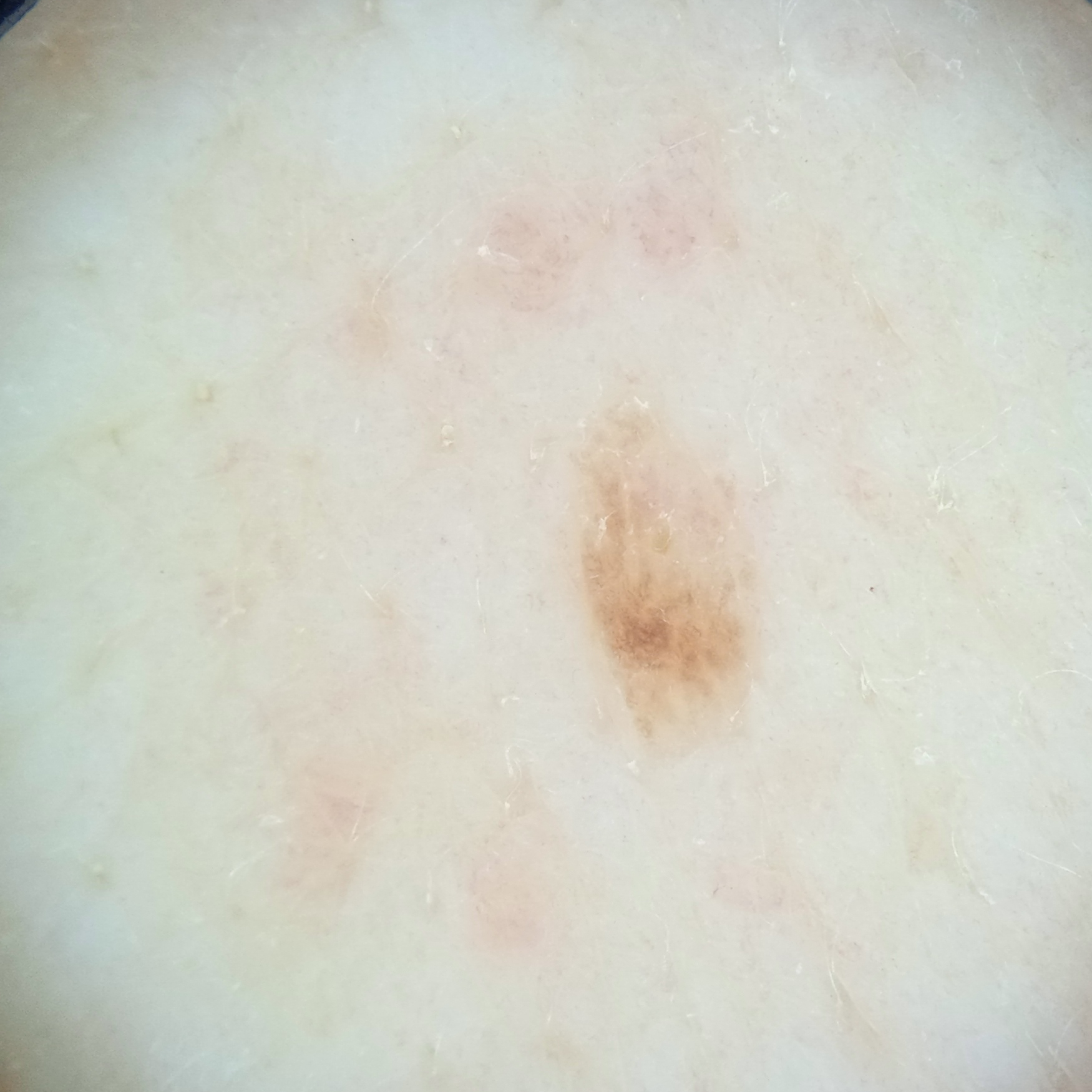subject = female, 71 years old | risk factors = a personal history of skin cancer, a personal history of cancer | imaging = dermoscopy | referral context = research study (no referral diagnosis) | body site = the back | diagnosis = seborrheic keratosis (dermatologist consensus).